A male subject aged 78-82; a clinical photograph of a skin lesion: 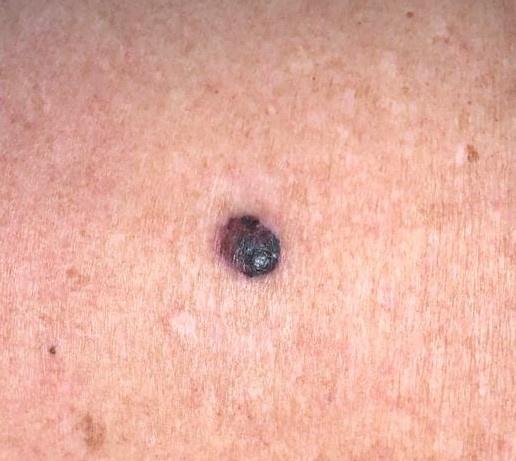The lesion involves the trunk (the posterior trunk). Histopathology confirmed a melanoma.